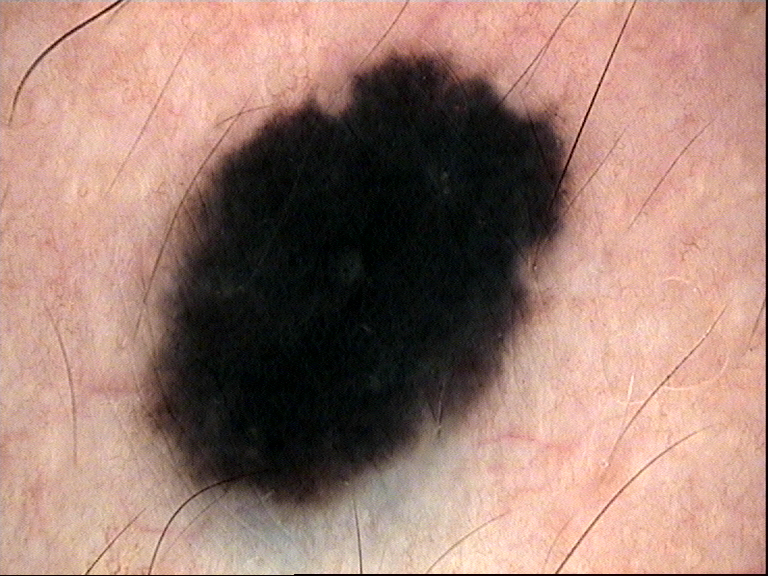diagnosis: blue nevus (expert consensus)